This image was taken at an angle. Located on the head or neck and arm.
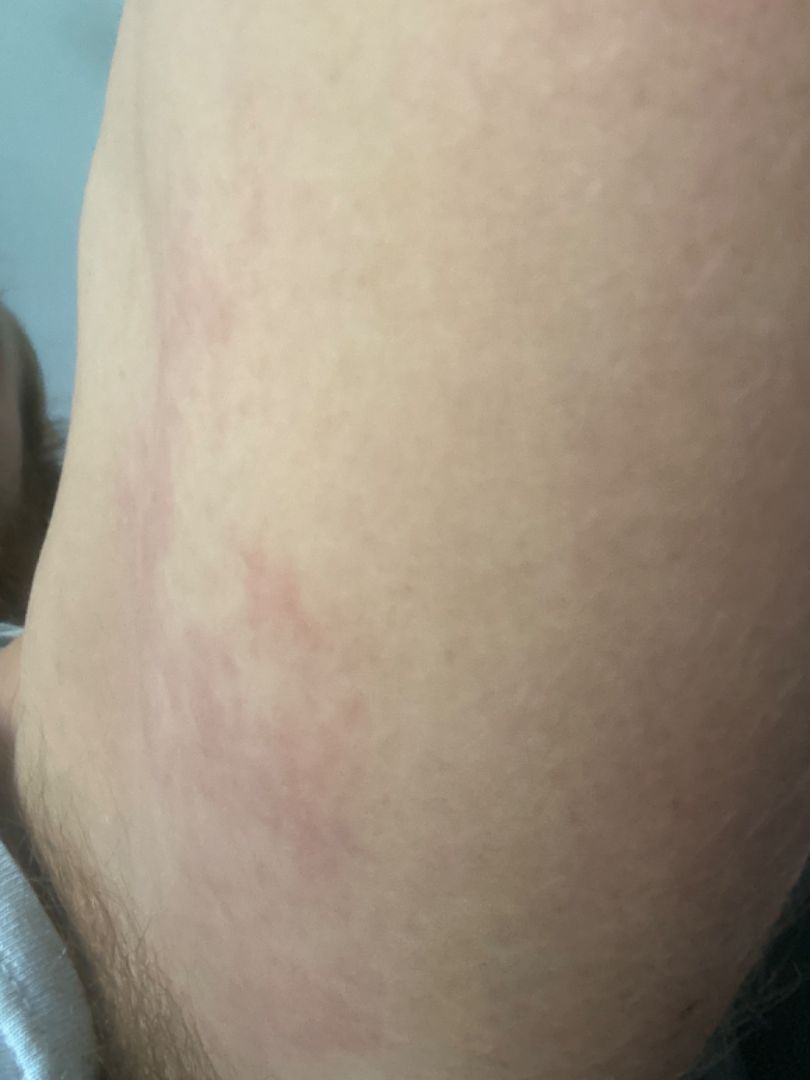assessment = indeterminate
patient-reported symptoms = itching, burning and bothersome appearance
self-categorized as = a rash
lesion texture = flat
onset = less than one week